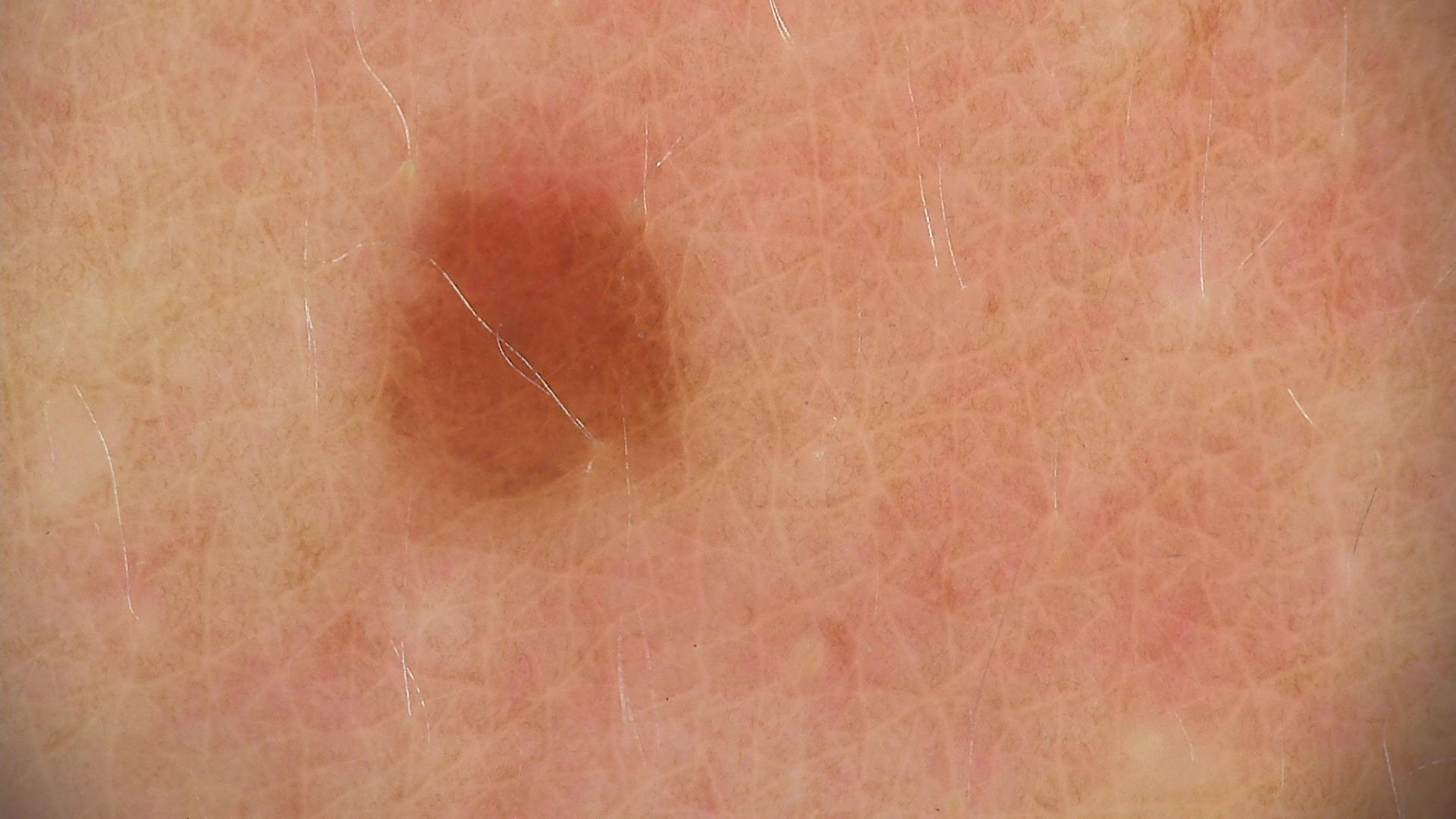| feature | finding |
|---|---|
| imaging | dermatoscopy |
| assessment | dysplastic junctional nevus (expert consensus) |